Recorded as Fitzpatrick III · the chart records pesticide exposure and alcohol use · a clinical photograph of a skin lesion · a male subject age 31:
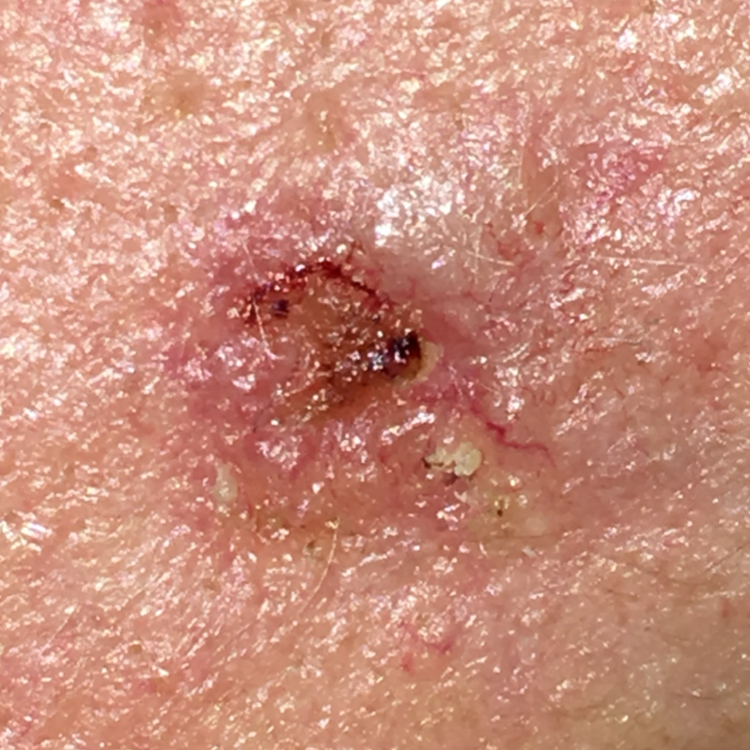The lesion involves the face.
The lesion measures approximately 10 × 7 mm.
By the patient's account, the lesion has bled, is elevated, and has grown, but has not changed.
Histopathological examination showed a basal cell carcinoma.